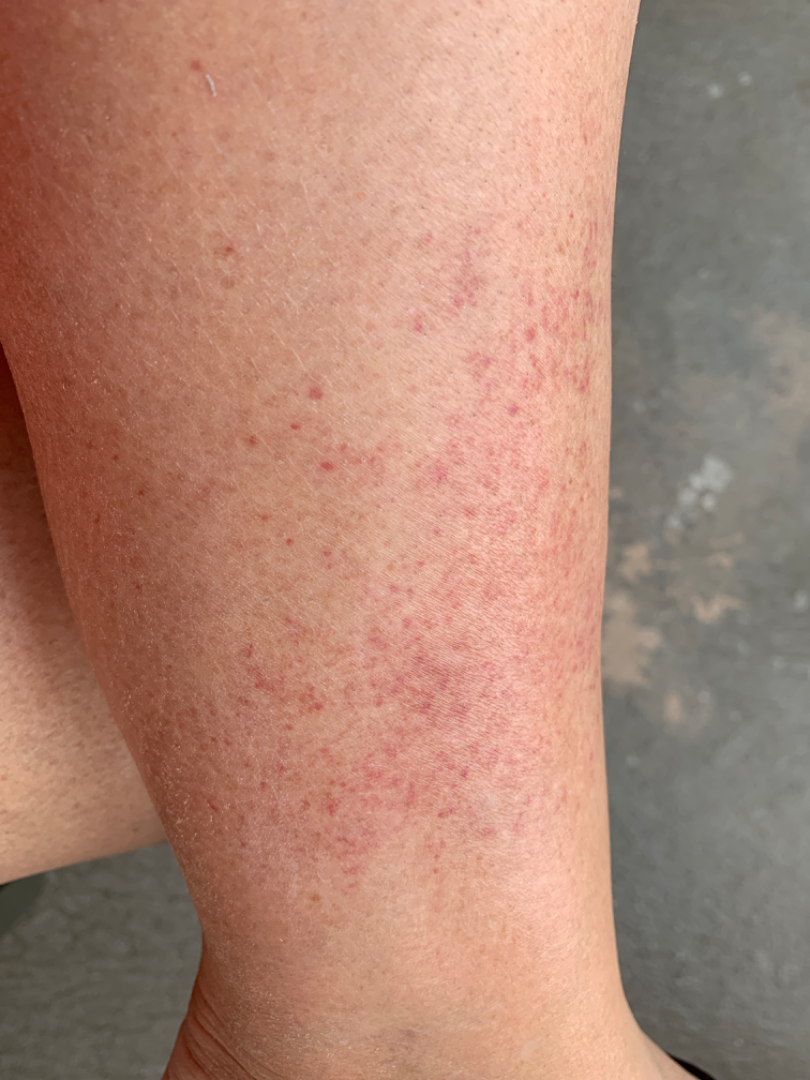History:
Female patient, age 60–69. Reported duration is less than one week. The patient indicates associated mouth sores. The lesion is described as flat. This is a close-up image. The leg is involved. The patient described the issue as a rash. No associated lesion symptoms were reported.
Impression:
The reviewing dermatologist's impression was: Pigmented purpuric eruption (67%); Leukocytoclastic Vasculitis (33%).